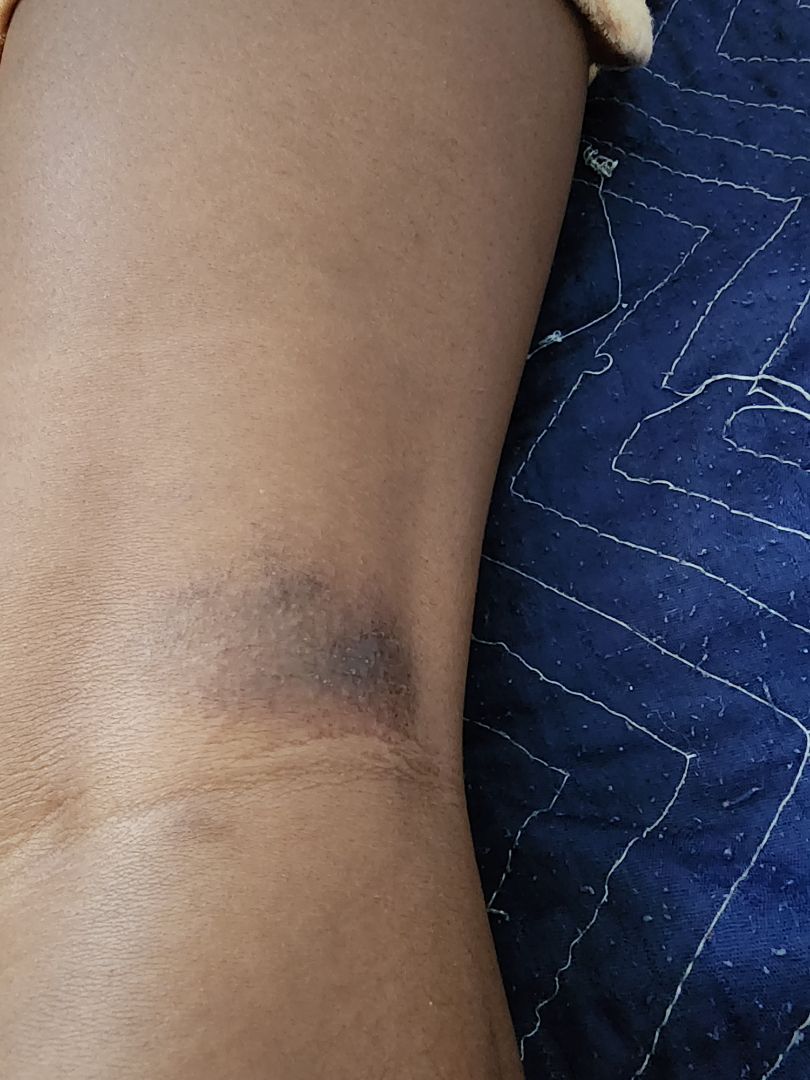Impression:
Single-reviewer assessment: the favored diagnosis is Lichen Simplex Chronicus; possibly Lichen planus/lichenoid eruption; a remote consideration is ecchymoses.